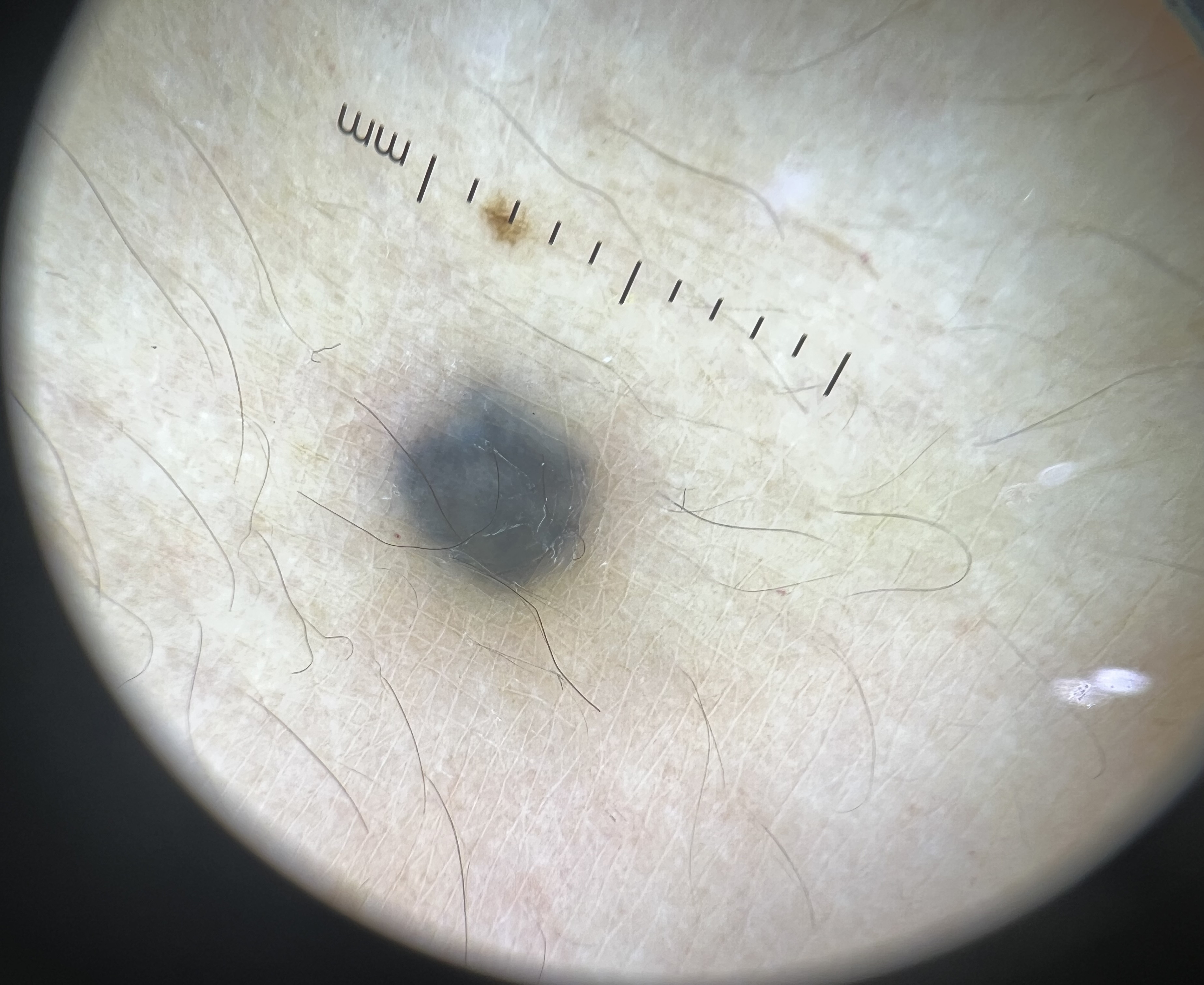Findings: Dermoscopy of a skin lesion. Impression: Diagnosed as a blue nevus.